A skin lesion imaged with a dermatoscope.
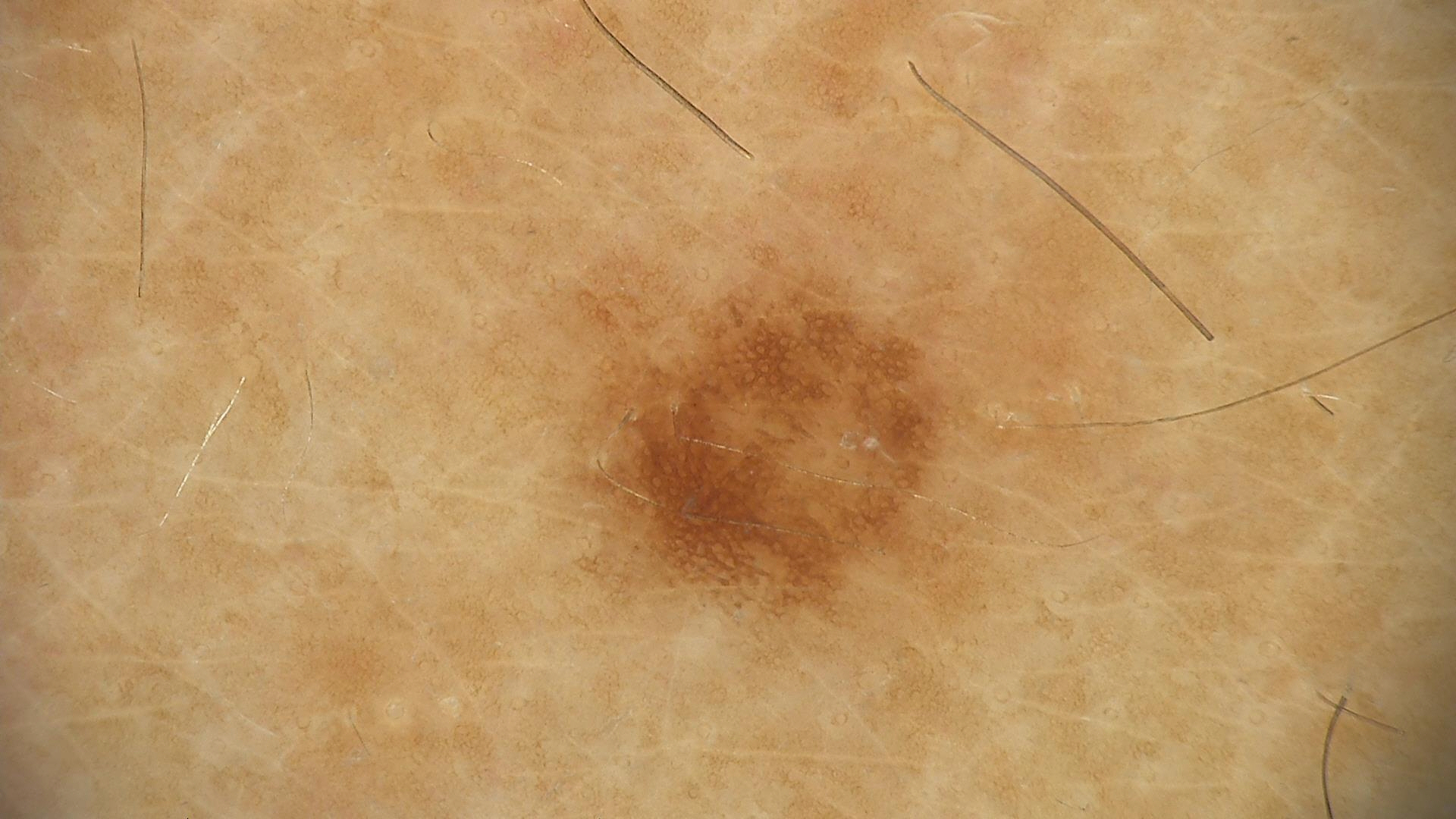class = dysplastic junctional nevus (expert consensus).